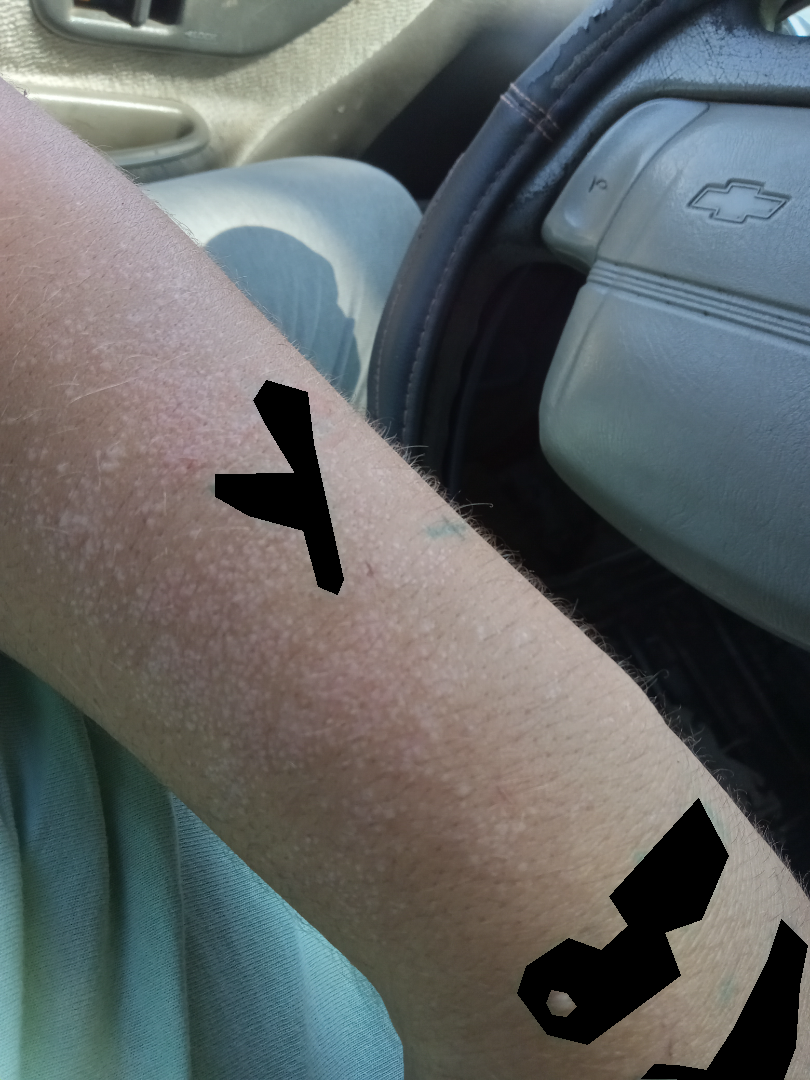Clinical context:
The affected area is the arm. Present for three to twelve months. An image taken at an angle. No relevant systemic symptoms. The lesion is associated with itching and pain.
Assessment:
A single dermatologist reviewed the case: consistent with Lichen planus/lichenoid eruption.